A female patient roughly 50 years of age — 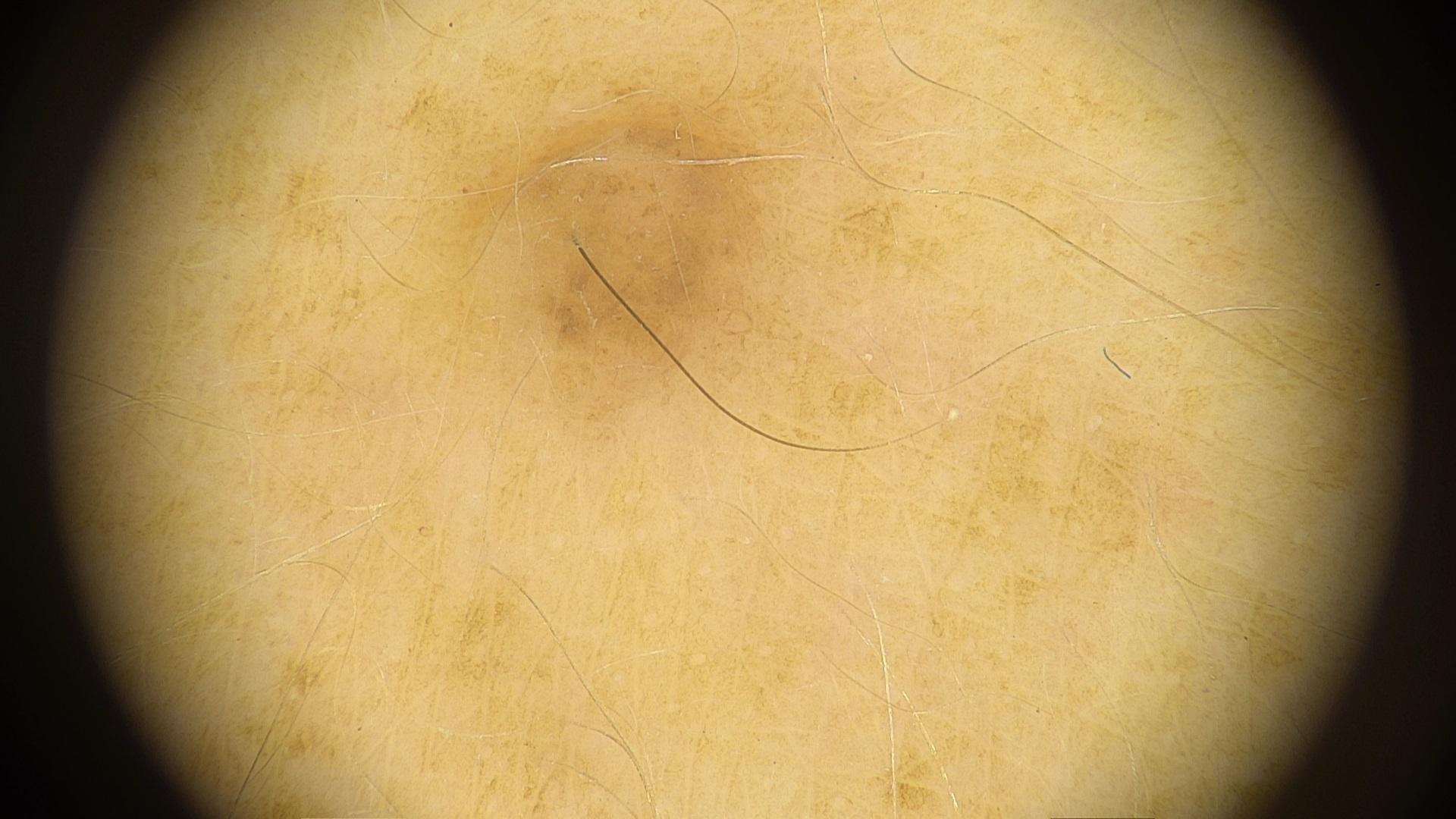Image and clinical context:
The lesion involves an upper extremity.
Conclusion:
Clinically diagnosed as a solar lentigo.